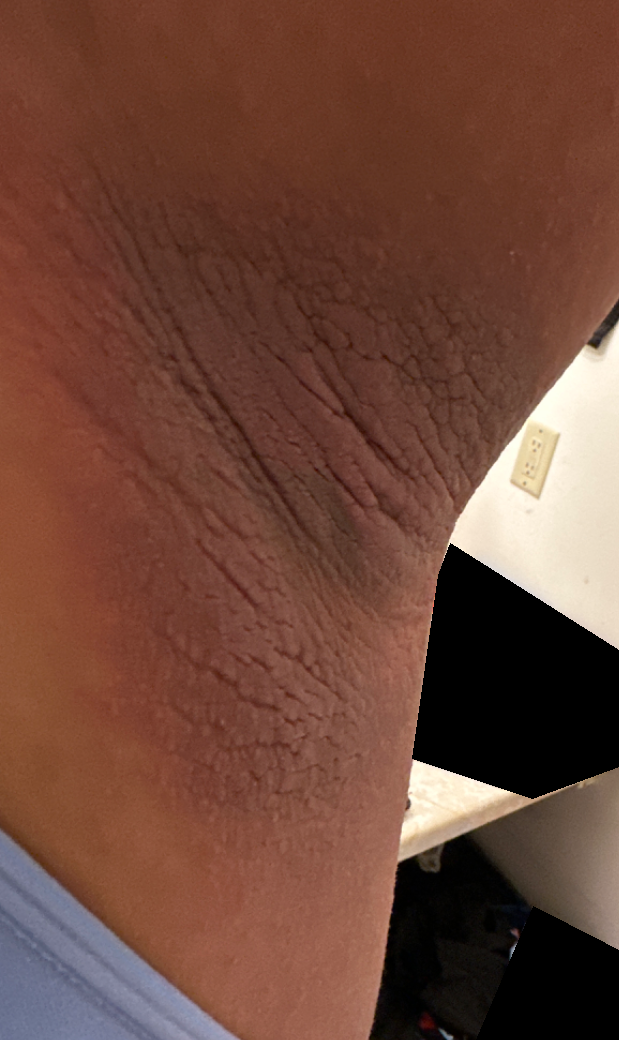Q: What conditions are considered?
A: consistent with Acanthosis nigricans